This image was taken at an angle.
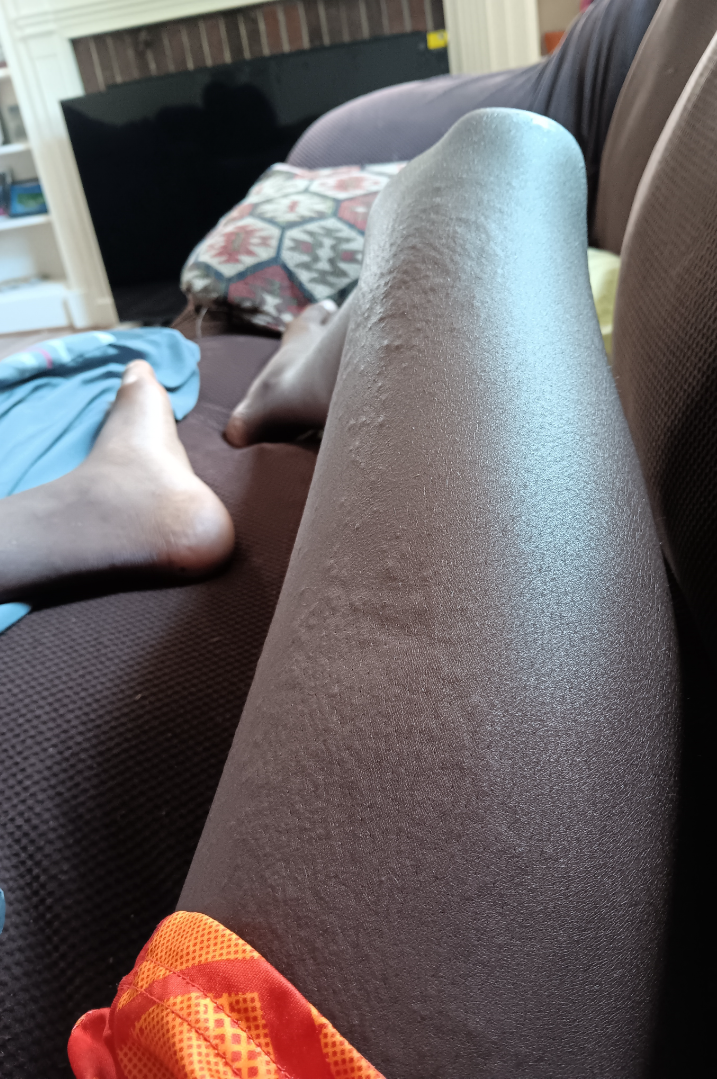The image was not sufficient for the reviewer to characterize the skin condition.
The lesion is associated with itching.